The contributor reports the lesion is raised or bumpy. Female subject, age 30–39. The photograph was taken at a distance. Fitzpatrick phototype III. The lesion is associated with pain. The leg is involved. The condition has been present for about one day. The patient described the issue as skin that appeared healthy to them — 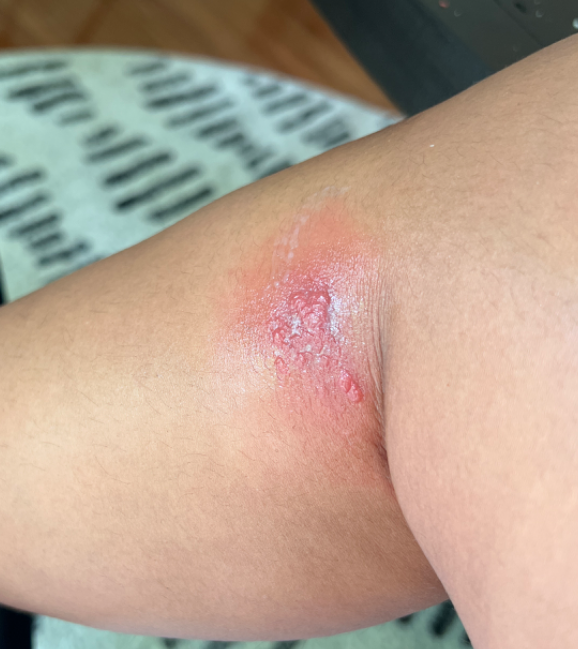Findings:
• diagnostic considerations · three dermatologists independently reviewed the case: most consistent with Cellulitis; the differential also includes Contact dermatitis; less likely is Infected eczema; less probable is Molluscum Contagiosum